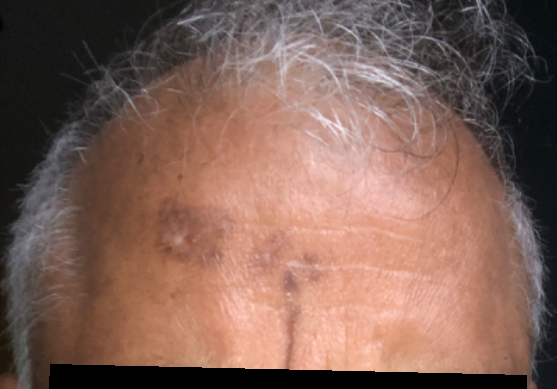{
  "texture": "flat",
  "shot_type": "close-up",
  "patient": "male",
  "duration": "three to twelve months",
  "symptoms": "darkening",
  "body_site": "head or neck",
  "differential": {
    "tied_lead": [
      "Prurigo nodularis",
      "Cutaneous lupus"
    ]
  }
}